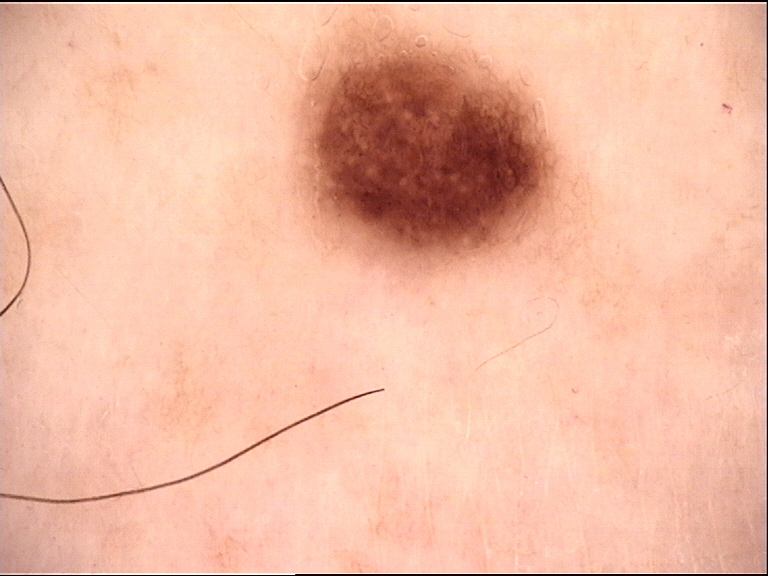Consistent with a benign lesion — a dysplastic junctional nevus.